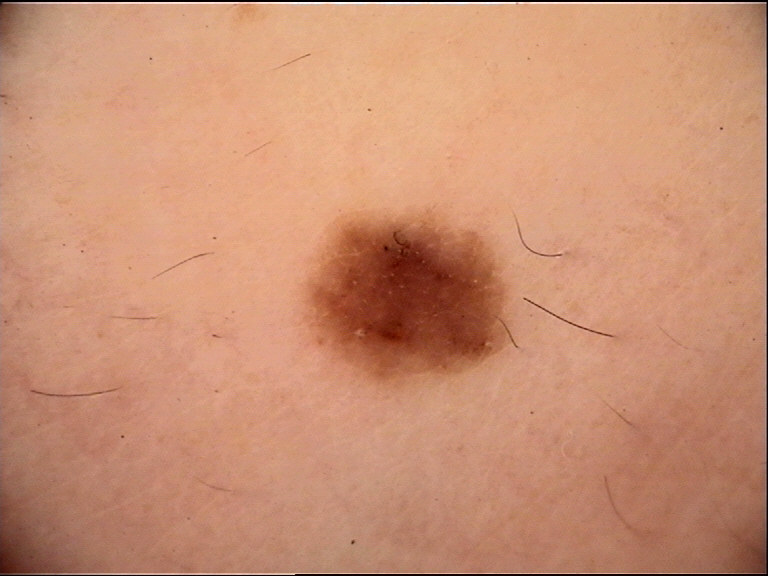{"diagnosis": {"name": "junctional nevus", "code": "jb", "malignancy": "benign", "super_class": "melanocytic", "confirmation": "expert consensus"}}